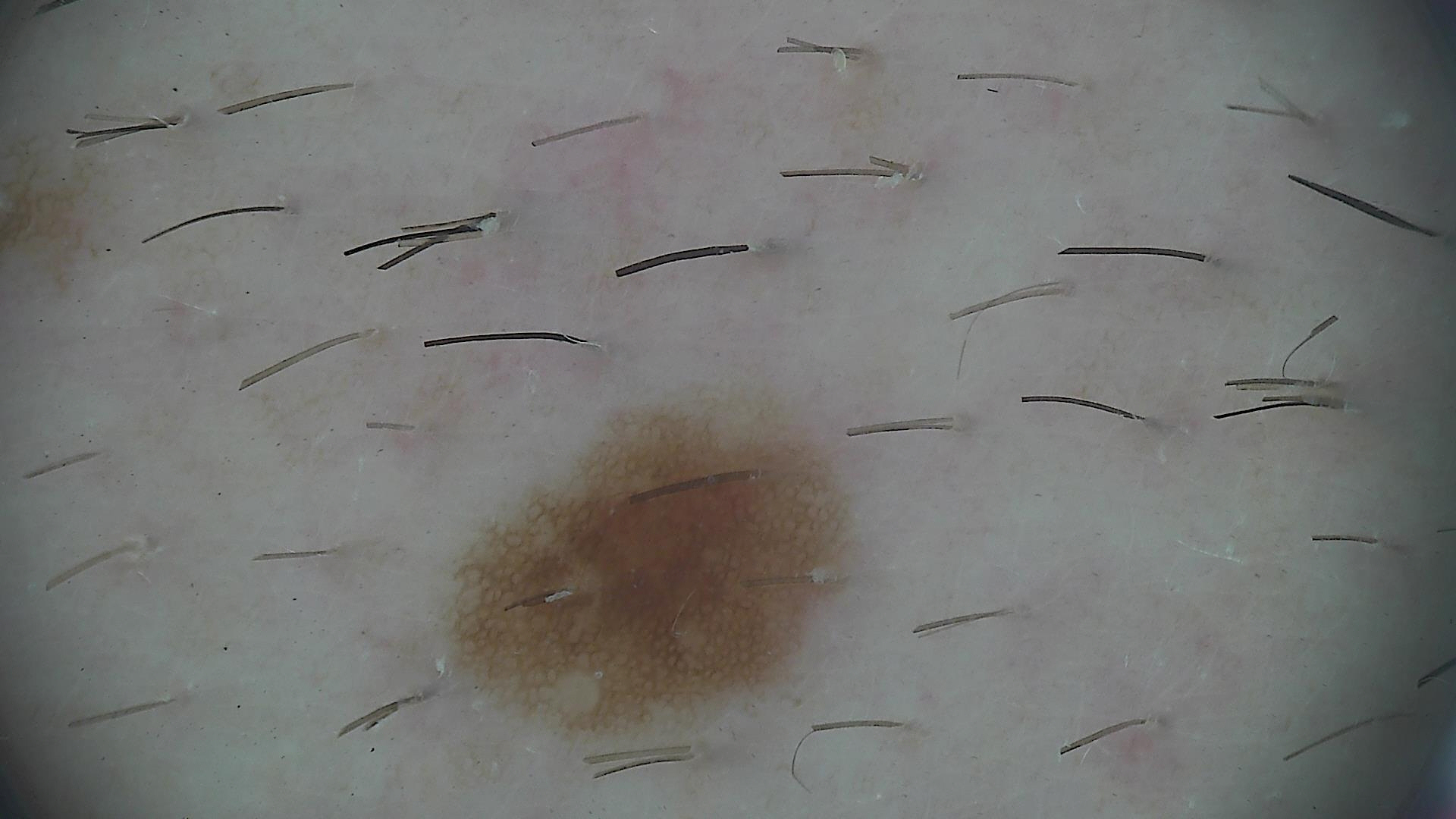modality = dermoscopy
label = dysplastic junctional nevus (expert consensus)